A dermoscopic photograph of a skin lesion.
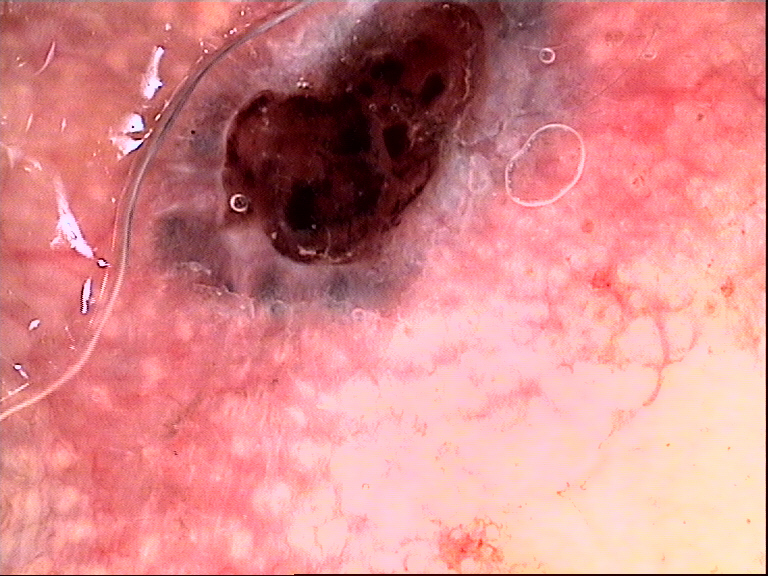lesion_type:
  main_class: keratinocytic
diagnosis:
  name: basal cell carcinoma
  code: bcc
  malignancy: malignant
  super_class: non-melanocytic
  confirmation: histopathology